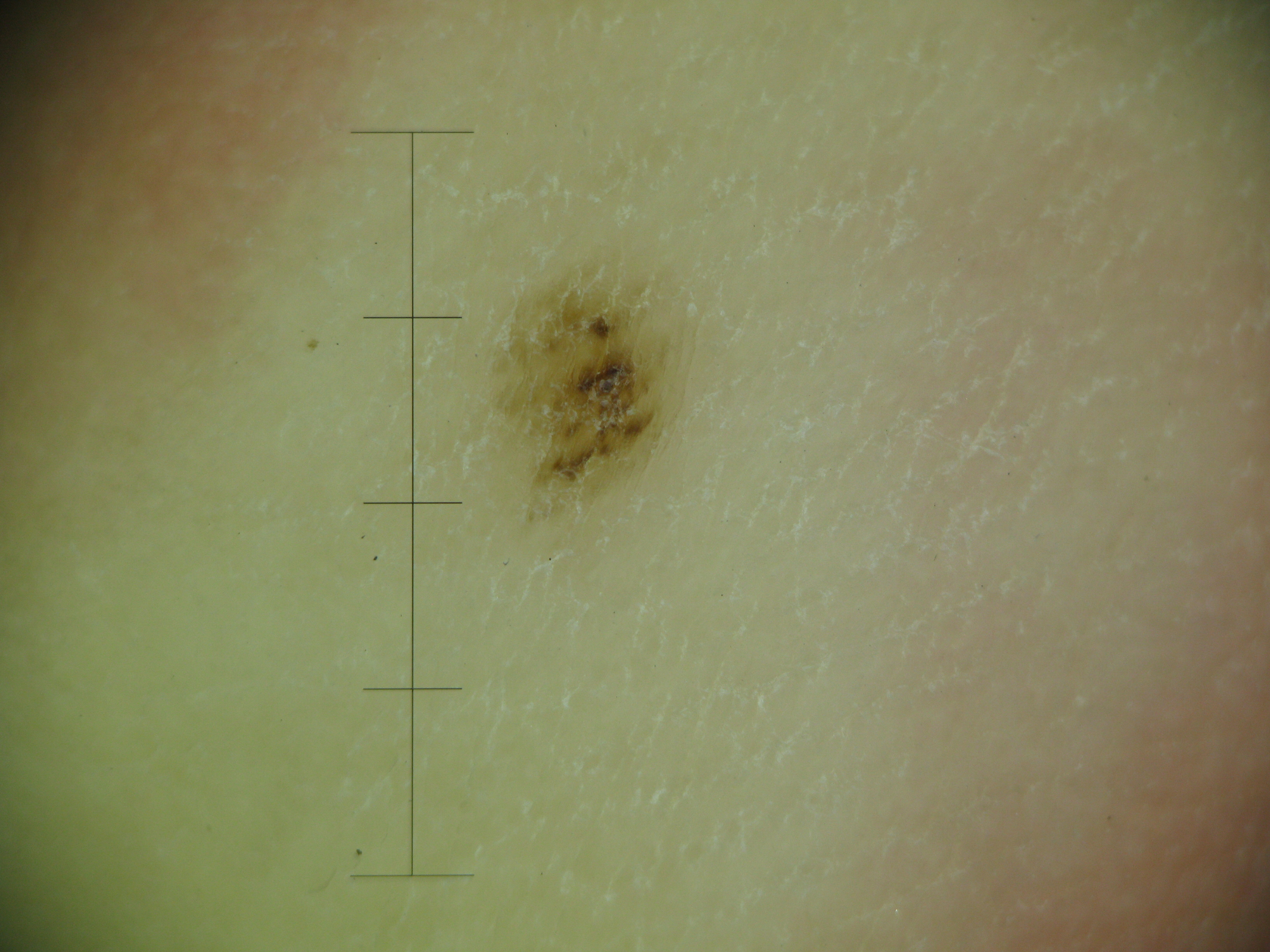classification: banal | label: acral junctional nevus (expert consensus).